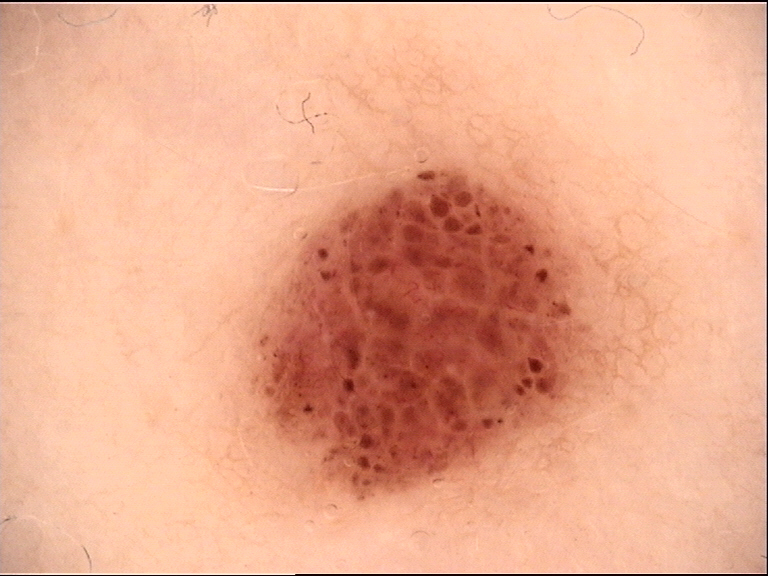Dermoscopy of a skin lesion. Consistent with a banal lesion — a compound nevus.